No relevant systemic symptoms; the leg is involved; the lesion is described as flat; female subject, age 30–39; the photo was captured at an angle; reported duration is about one day; symptoms reported: bothersome appearance; self-categorized by the patient as a rash:
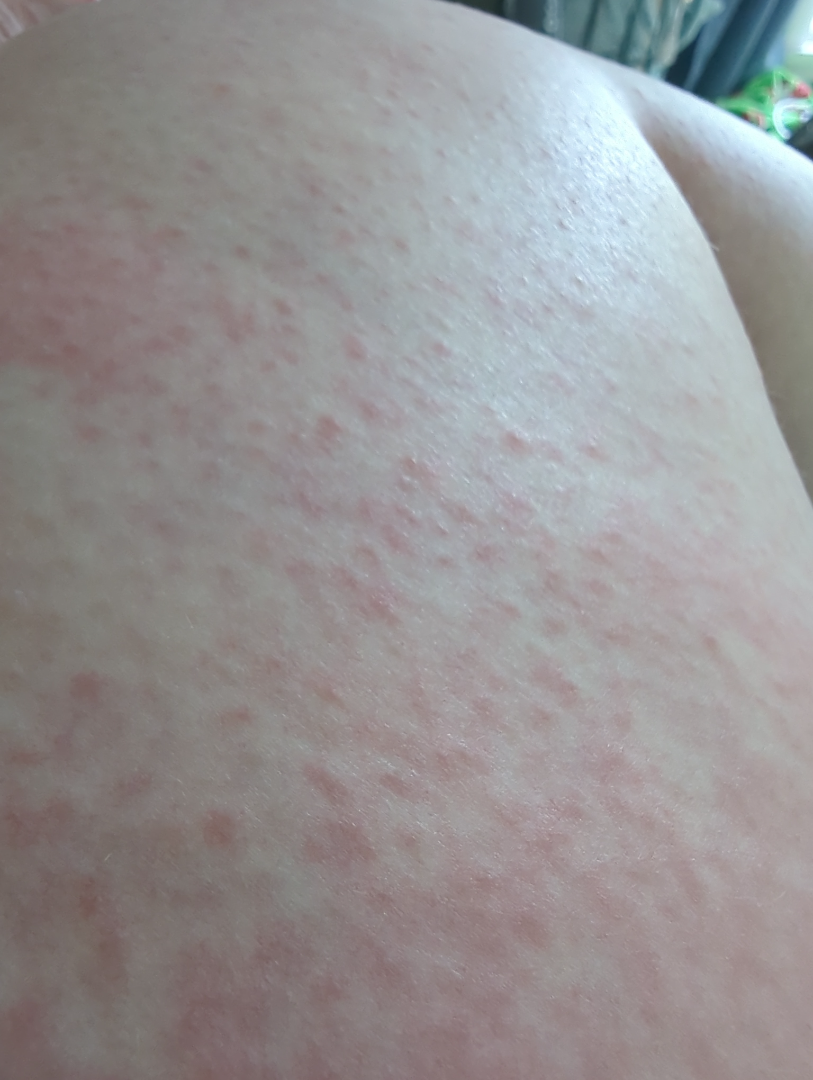On photographic review: Eczema and Drug Rash were each considered, in no particular order; a more distant consideration is Viral Exanthem; lower on the differential is Hypersensitivity.